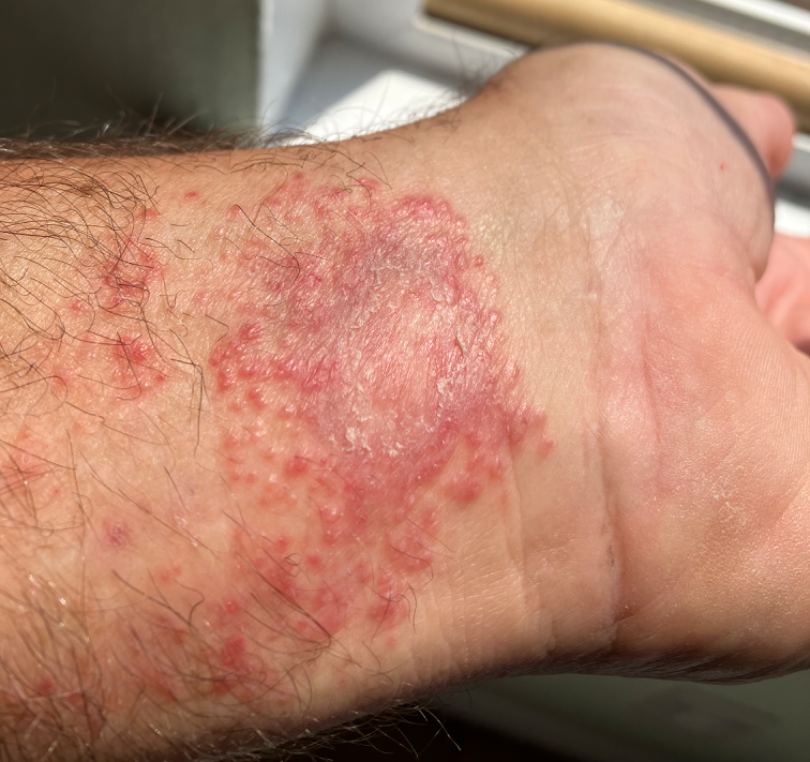<case>
  <shot_type>close-up</shot_type>
  <differential>Allergic Contact Dermatitis</differential>
</case>